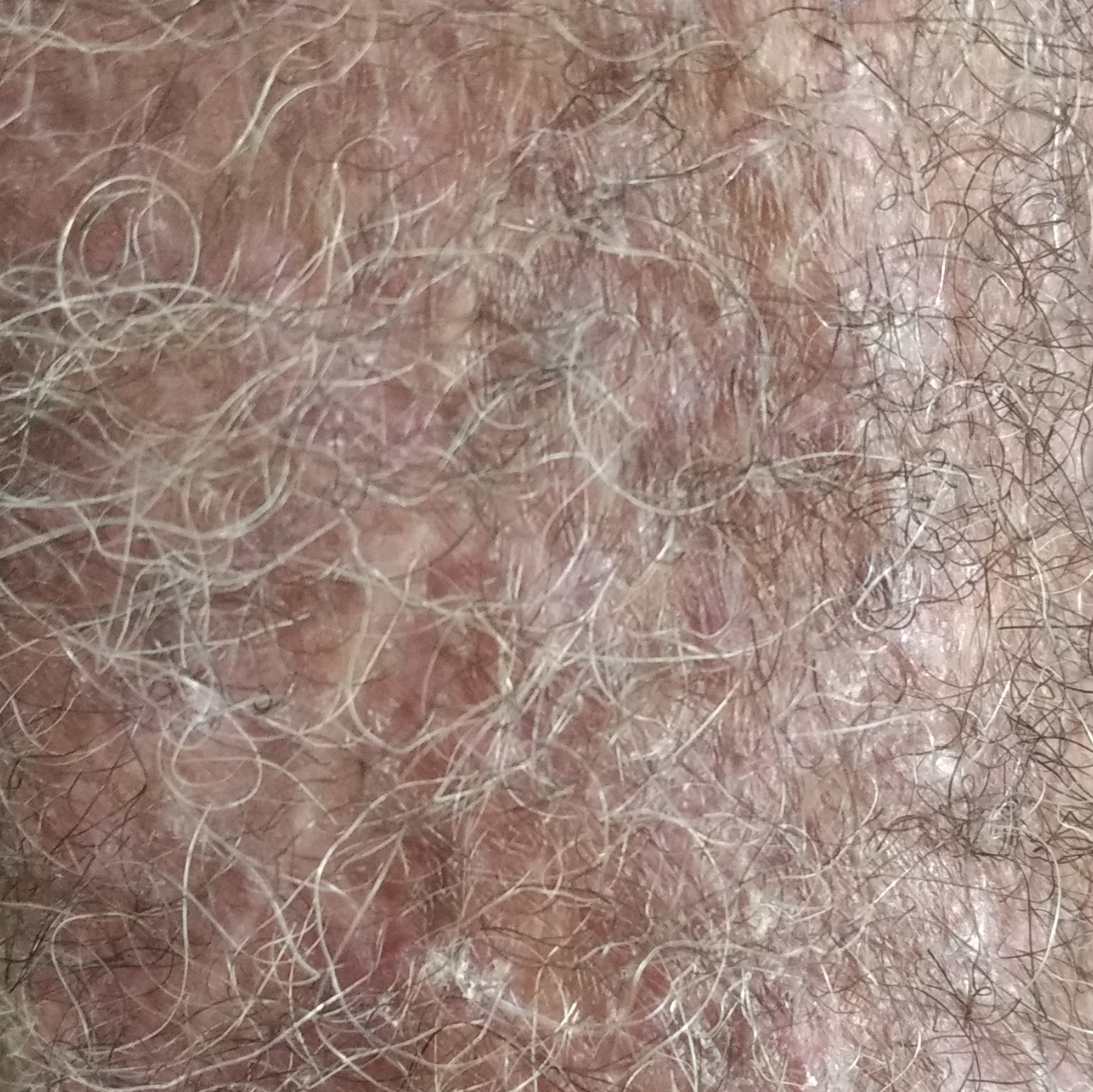Q: Any relevant history?
A: alcohol use, pesticide exposure
Q: Tell me about the patient.
A: male, 67 years old
Q: Skin phototype?
A: III
Q: What is the anatomic site?
A: a forearm
Q: What does the patient describe?
A: itching / no bleeding, no change in appearance
Q: What is the diagnosis?
A: actinic keratosis (clinical consensus)